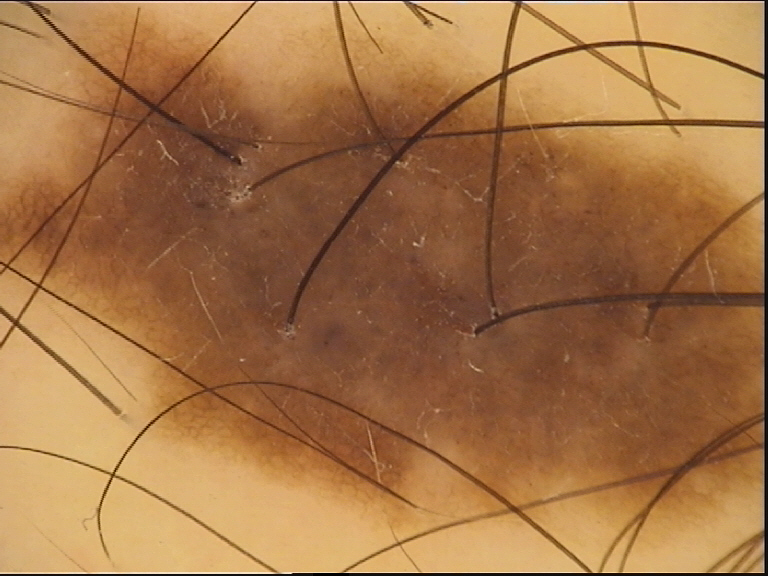Q: What is the diagnosis?
A: dysplastic compound nevus (expert consensus)